This image was taken at a distance:
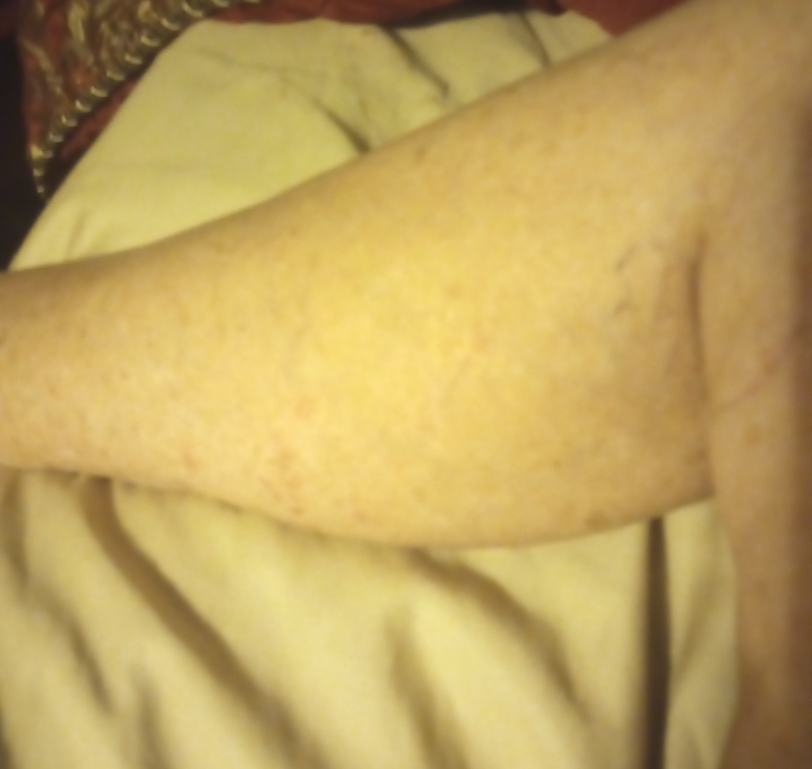The reviewing dermatologist was unable to assign a differential diagnosis from the image.